A dermoscopic photograph of a skin lesion: 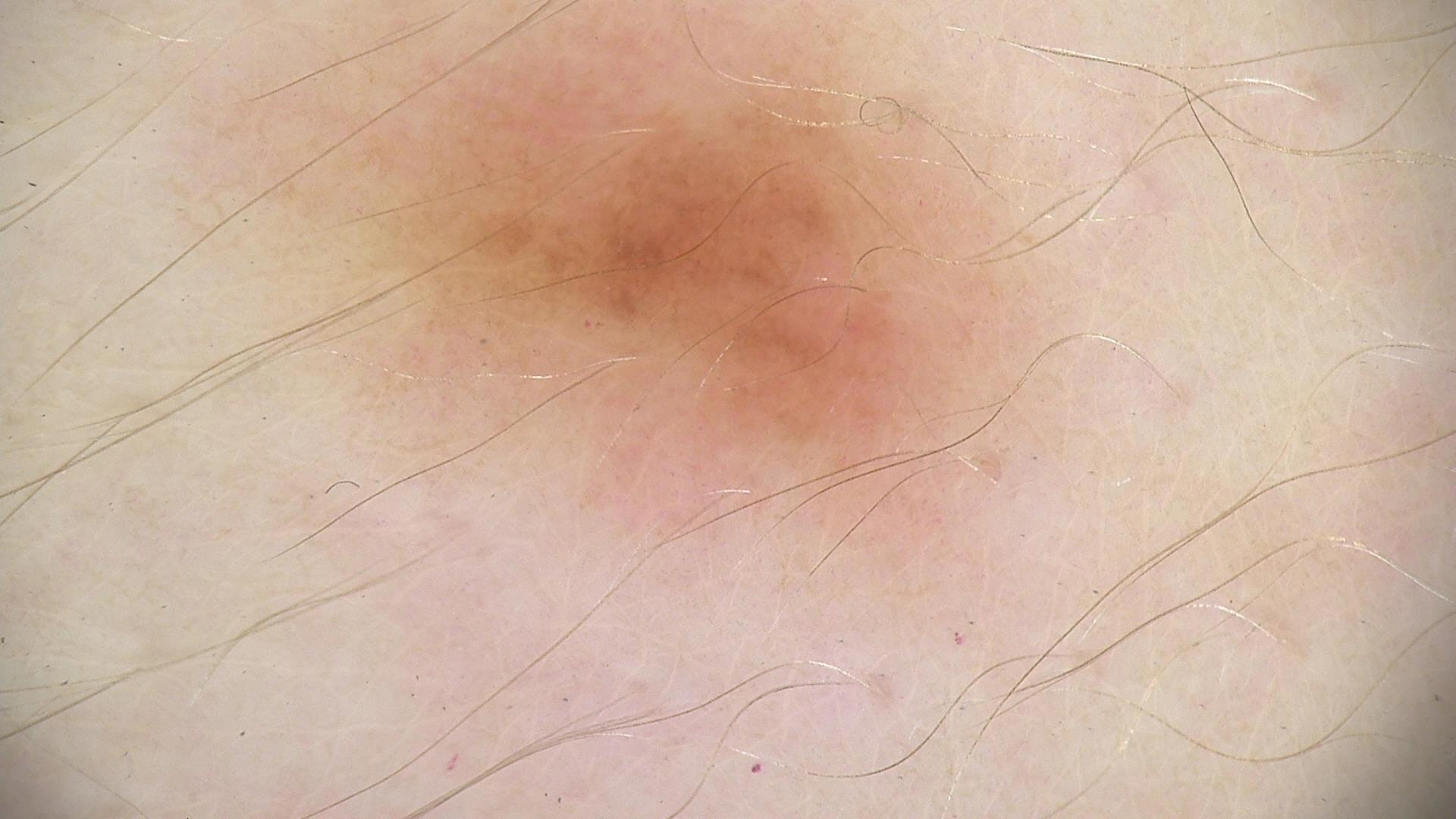Case:
* class — dysplastic junctional nevus (expert consensus)